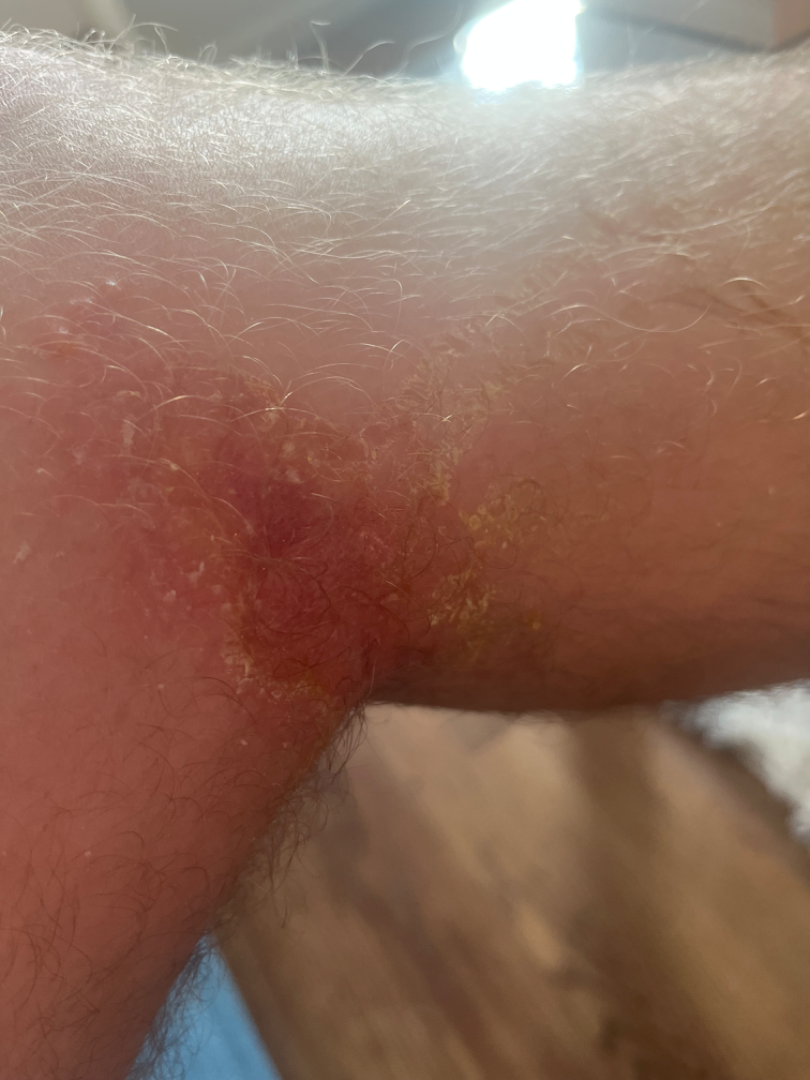On photographic review by a dermatologist: Insect Bite (favored).